A dermoscopic image of a skin lesion: 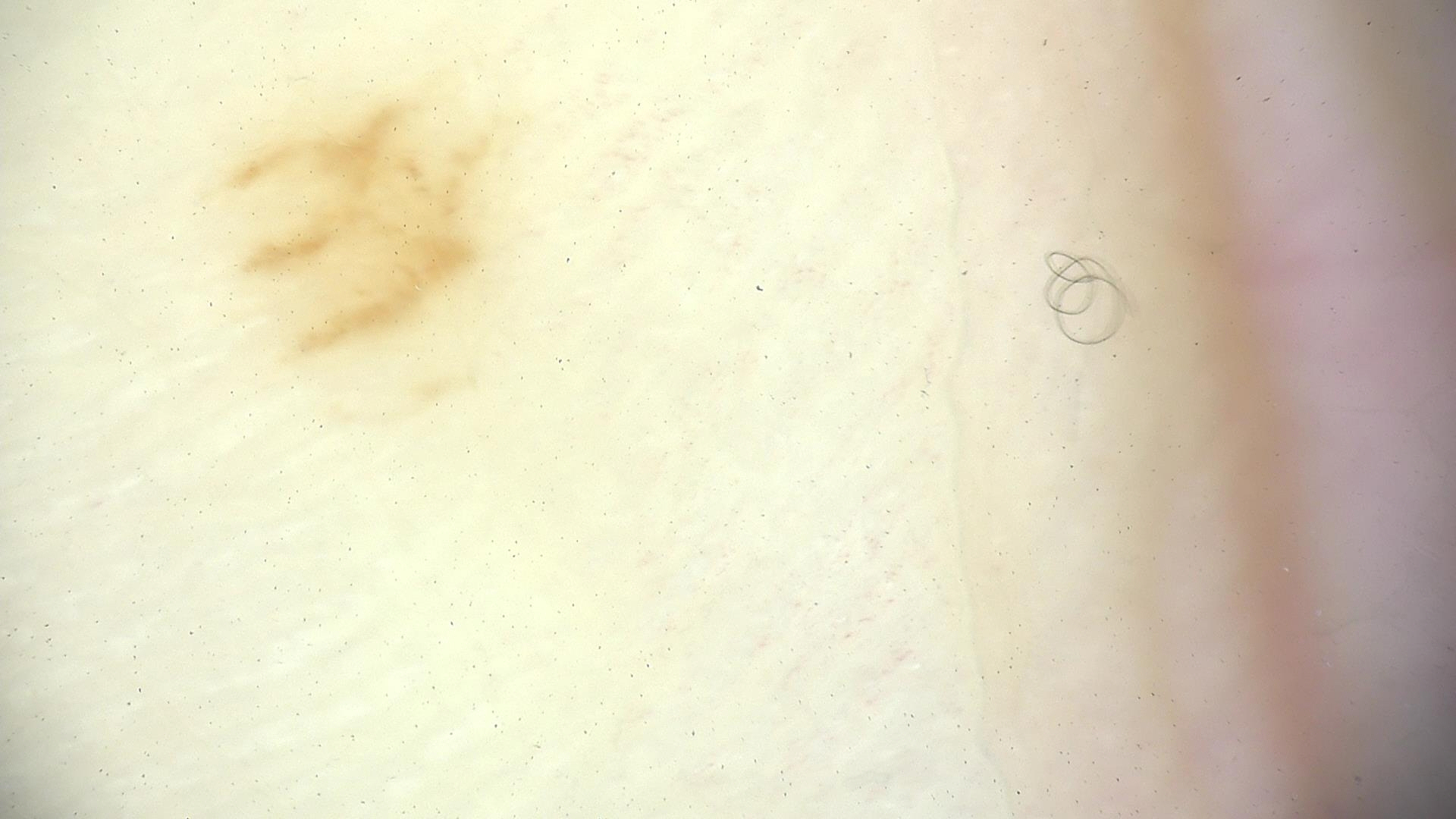{"diagnosis": {"name": "acral dysplastic junctional nevus", "code": "ajd", "malignancy": "benign", "super_class": "melanocytic", "confirmation": "expert consensus"}}